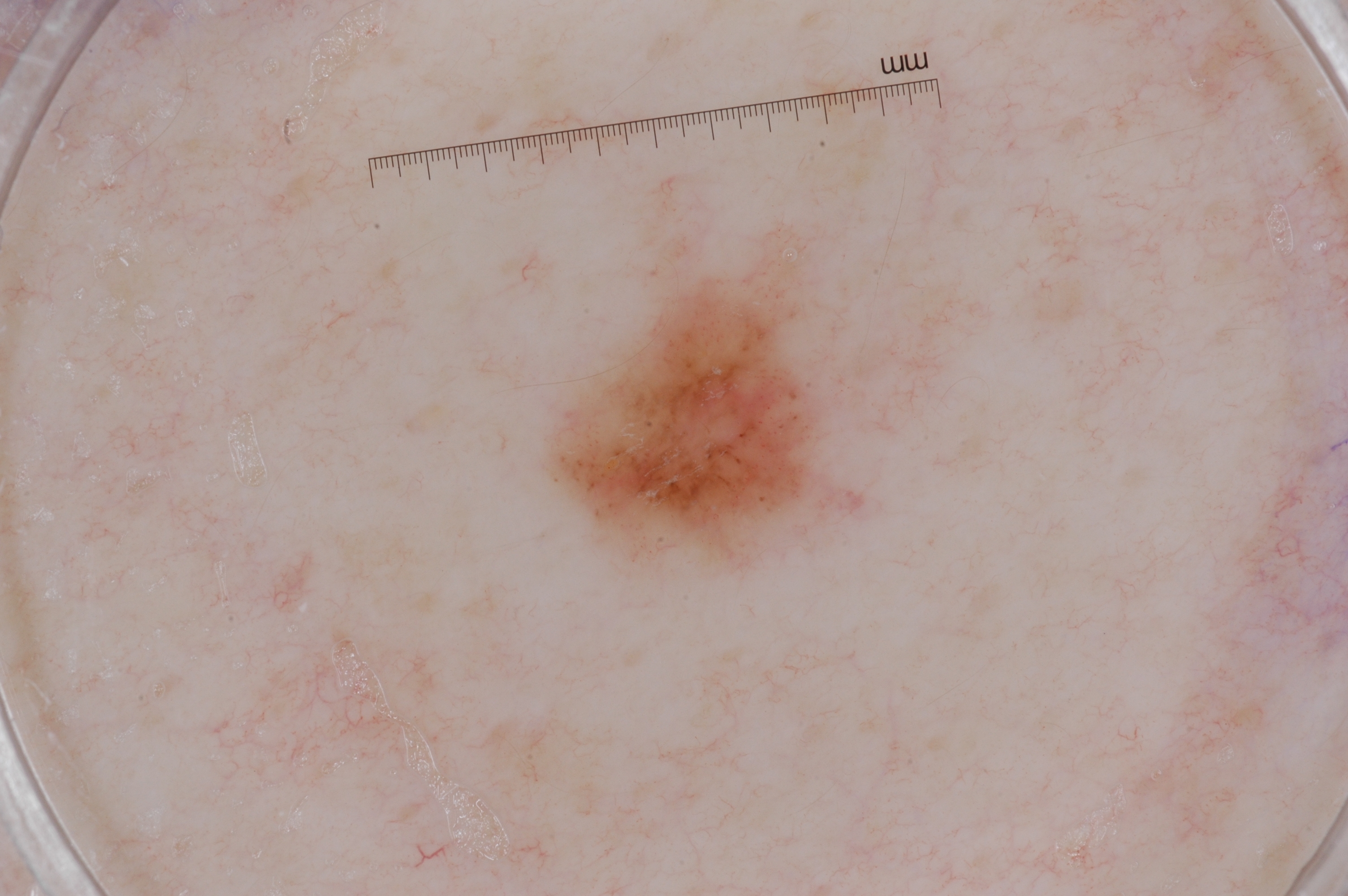{
  "image": {
    "modality": "dermoscopy"
  },
  "dermoscopic_features": {
    "present": [],
    "absent": [
      "milia-like cysts",
      "streaks",
      "negative network",
      "pigment network"
    ]
  },
  "lesion_location": {
    "bbox_xyxy": [
      558,
      266,
      853,
      567
    ]
  },
  "diagnosis": {
    "name": "melanocytic nevus",
    "malignancy": "benign",
    "lineage": "melanocytic",
    "provenance": "clinical"
  }
}